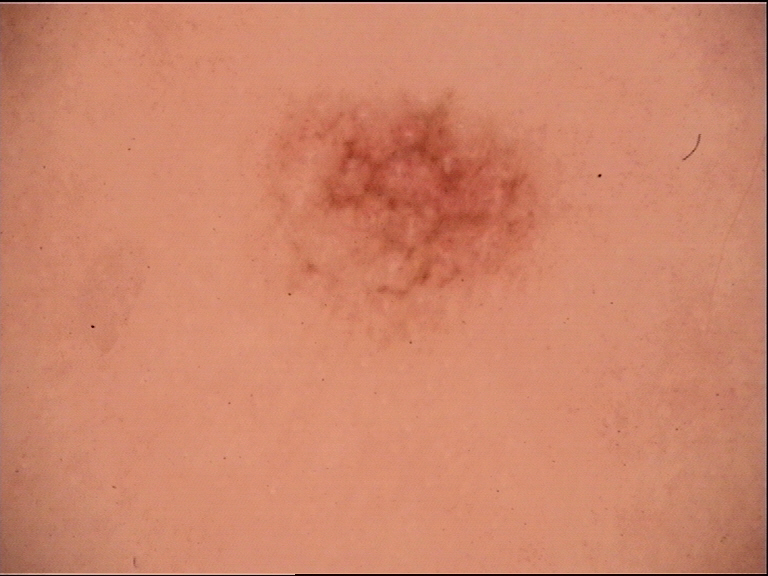The diagnosis was an acral dysplastic junctional nevus.